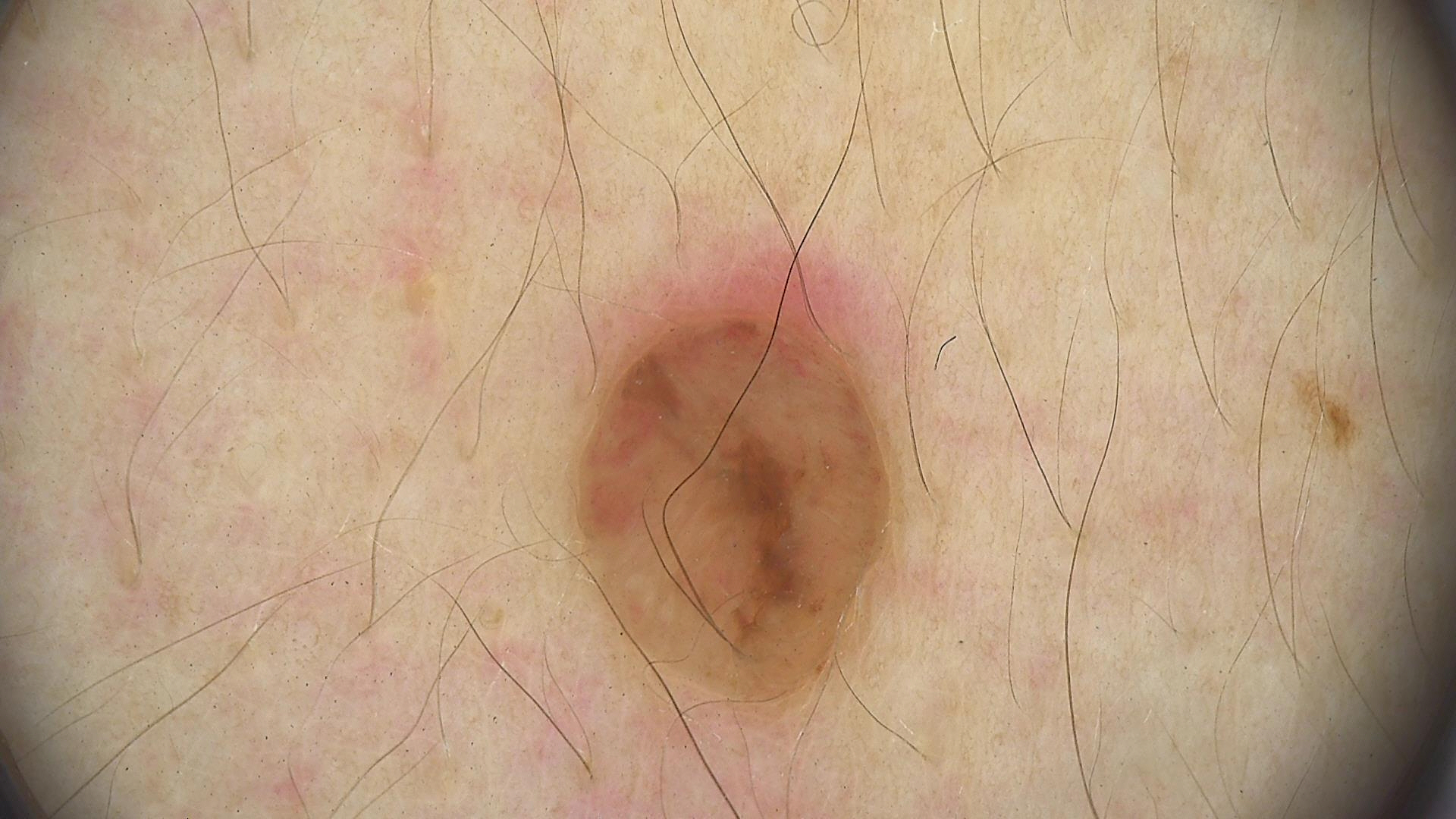A dermoscopic image of a skin lesion. Diagnosed as a banal lesion — a dermal nevus.